A clinical photograph showing a skin lesion; the chart notes pesticide exposure, prior skin cancer (patient or family), prior malignancy (patient or family), and no tobacco use; recorded as FST II; a male patient age 68:
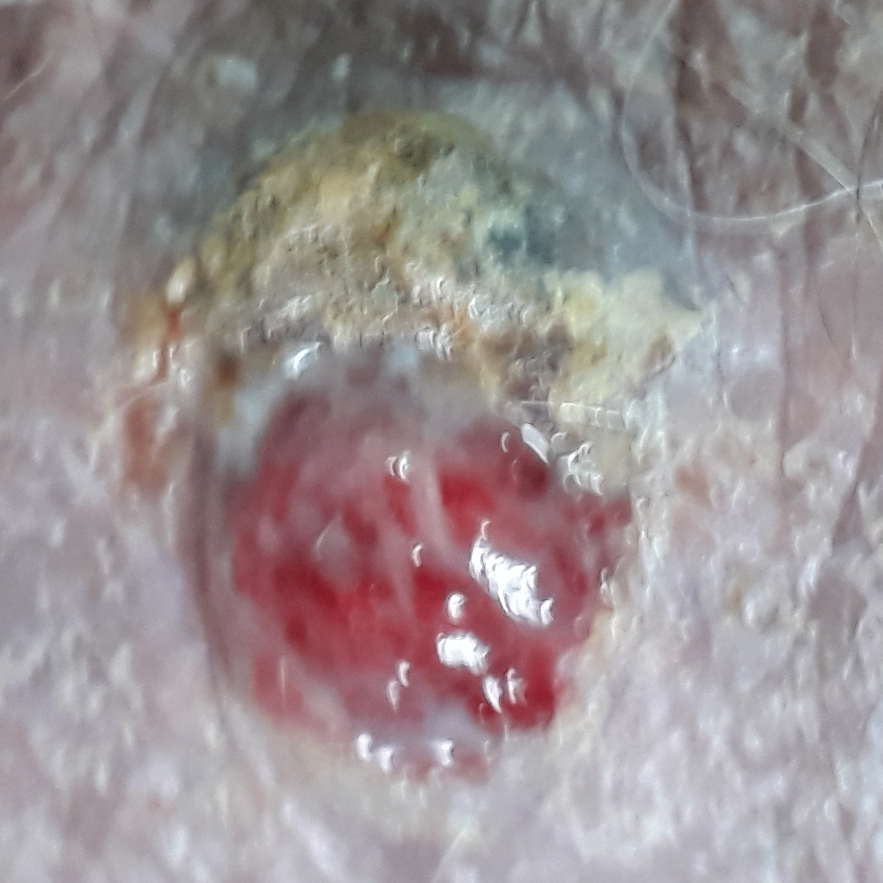The lesion measures 11 × 7 mm.
The patient reports that the lesion hurts, has changed, itches, has grown, has bled, and is elevated.
The biopsy diagnosis was a malignant skin lesion — a squamous cell carcinoma.